The subject is a female in their 50s · a dermoscopic close-up of a skin lesion — 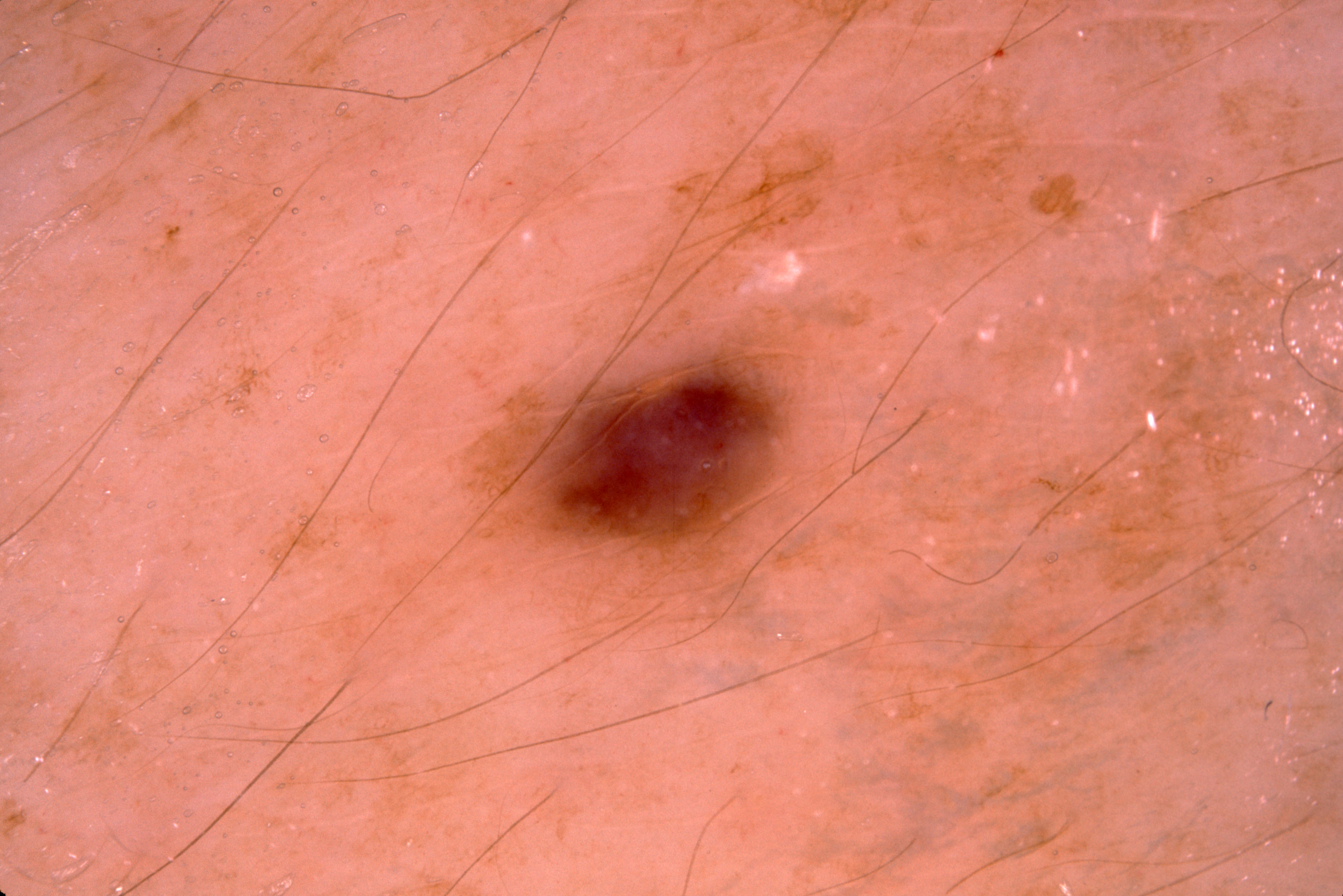In (x1, y1, x2, y2) order, lesion location: 459, 313, 848, 617. The lesion occupies roughly 7% of the field. Dermoscopic review identifies no negative network, milia-like cysts, pigment network, or streaks. Consistent with a melanocytic nevus, a benign skin lesion.